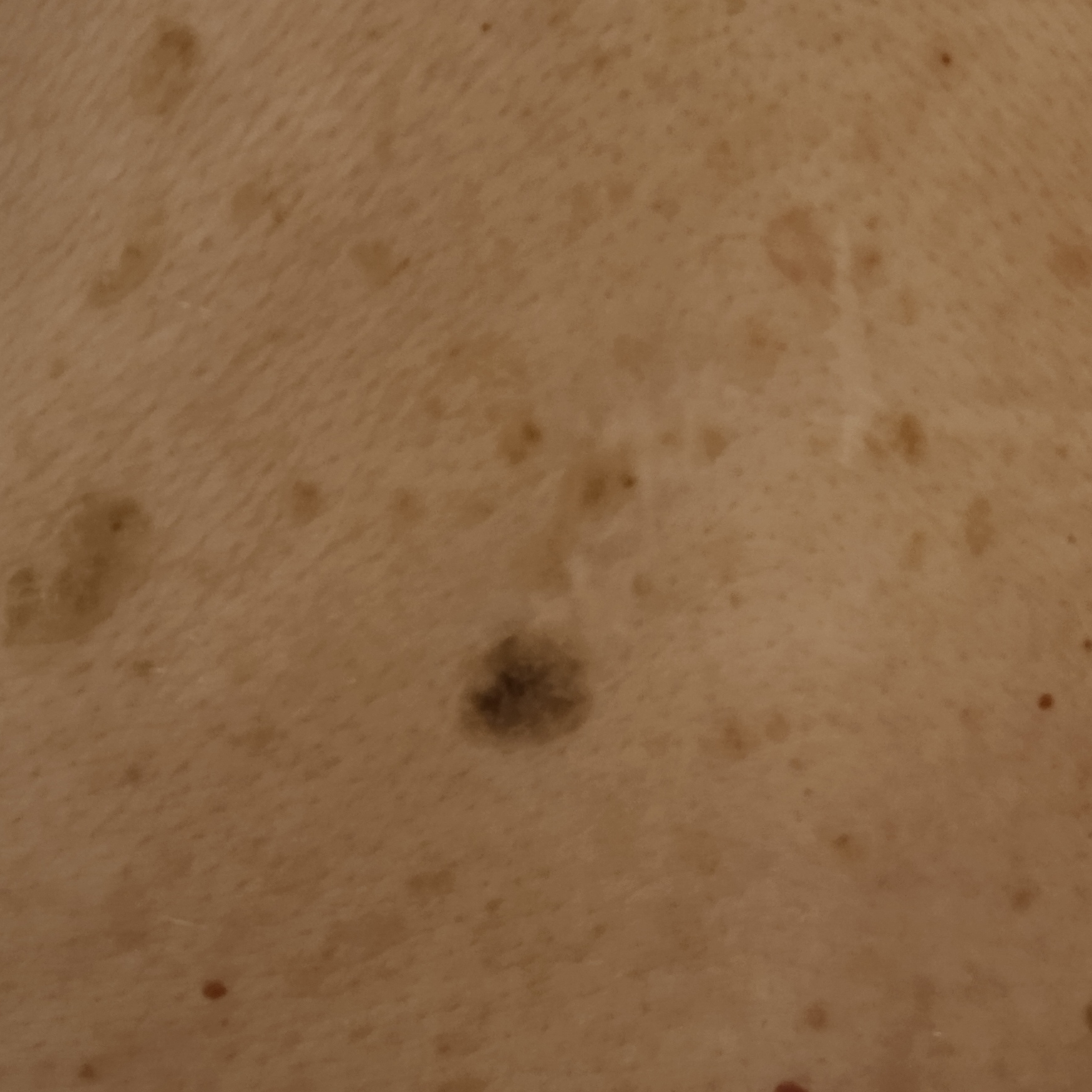Clinical context: The patient says their skin reddens with sun exposure. Imaged for a research study, with no referral diagnosis recorded. A macroscopic clinical photograph of a skin lesion. A male subject aged 78. The patient reports a personal history of cancer, no sunbed use, and no prior organ transplant. The patient describes having few moles overall. The lesion is located on the back. The lesion measures approximately 11 mm. Assessment: Dermatologist review favored a seborrheic keratosis.